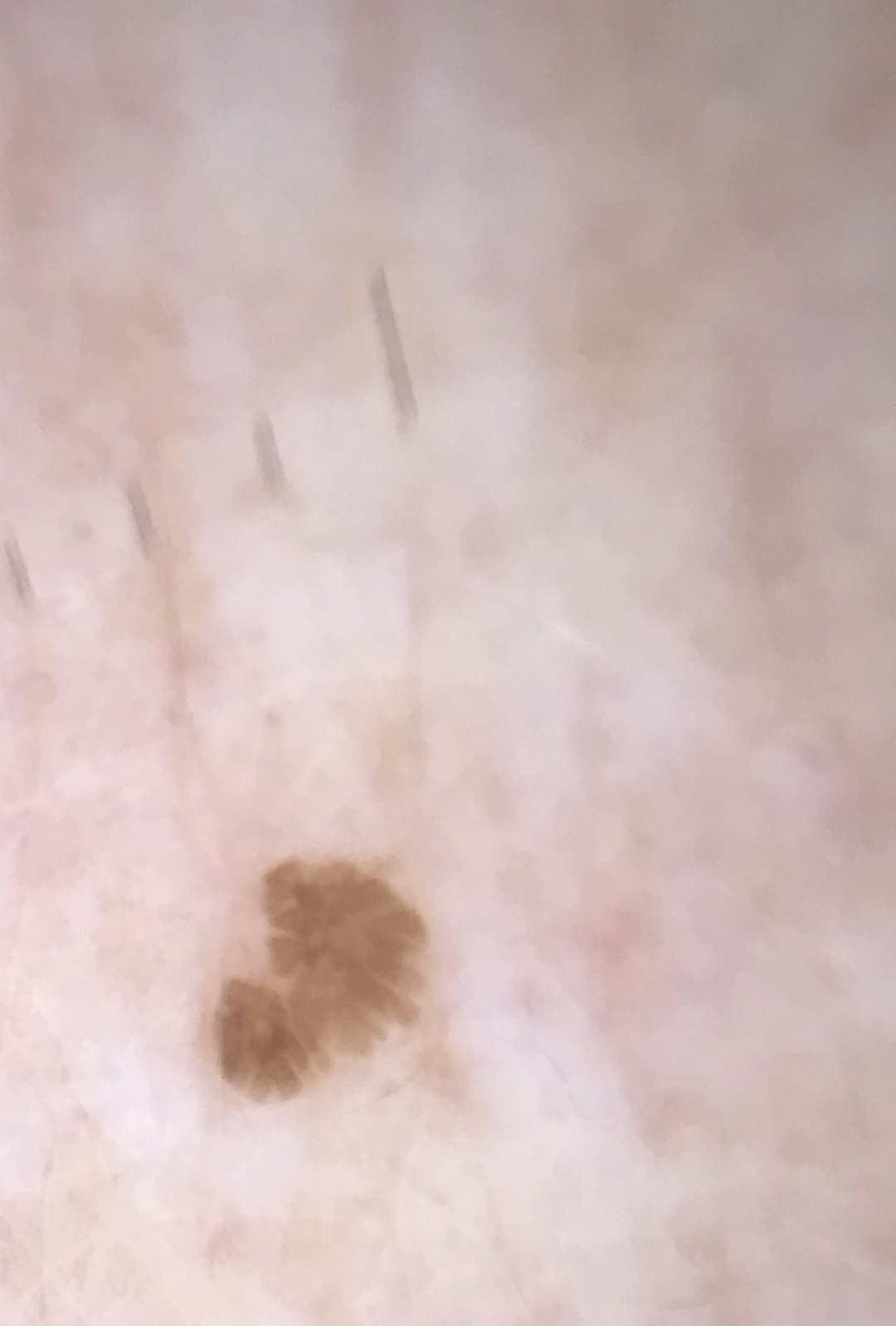This is a keratinocytic lesion.
Labeled as a seborrheic keratosis.